A female patient aged 53-57. The chart records no prior melanoma and no first-degree relative with melanoma. The patient is skin type IV — 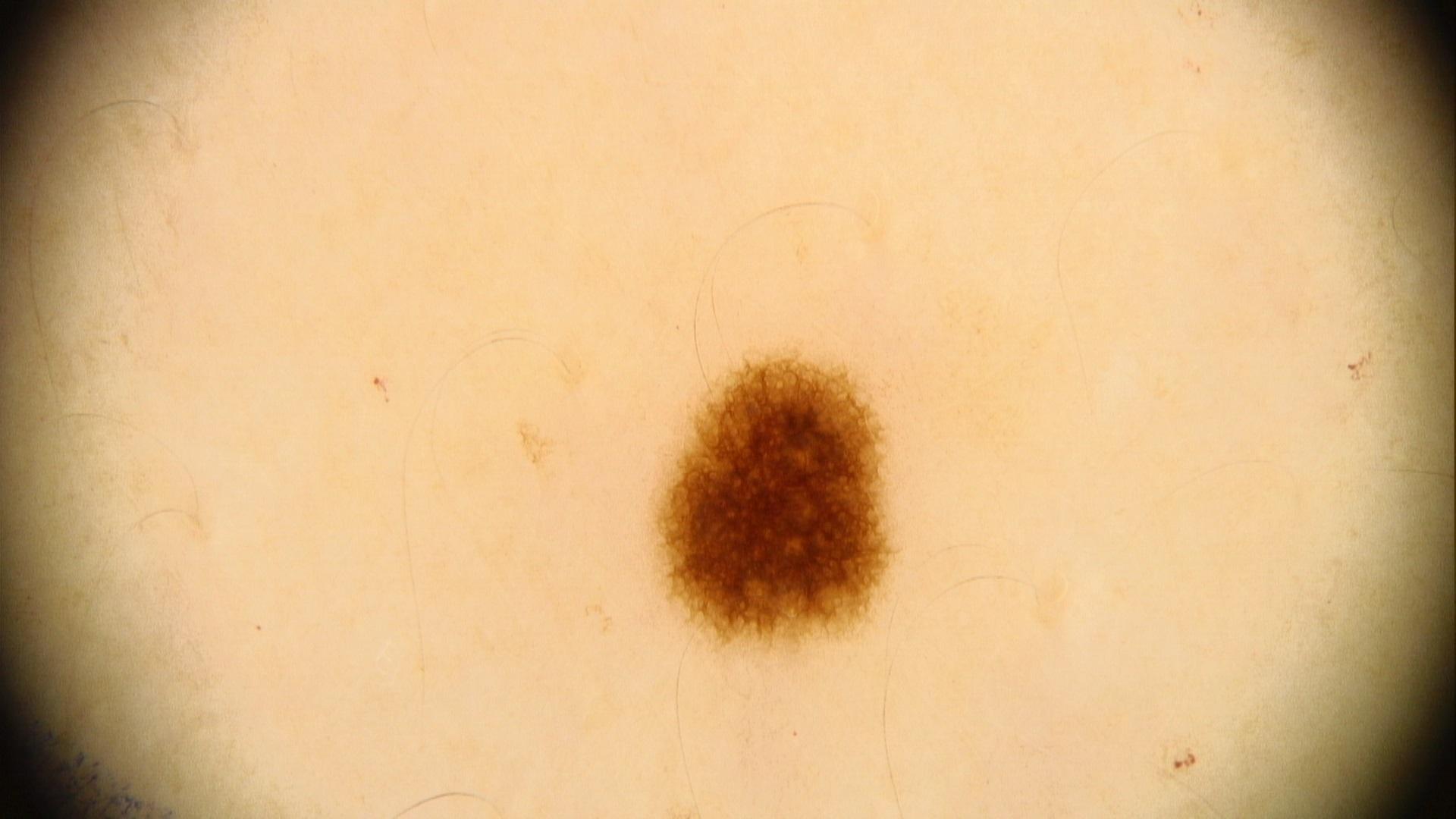Notes:
• site · the anterior trunk
• diagnosis · Nevus (clinical impression)